A dermoscopic image of a skin lesion: 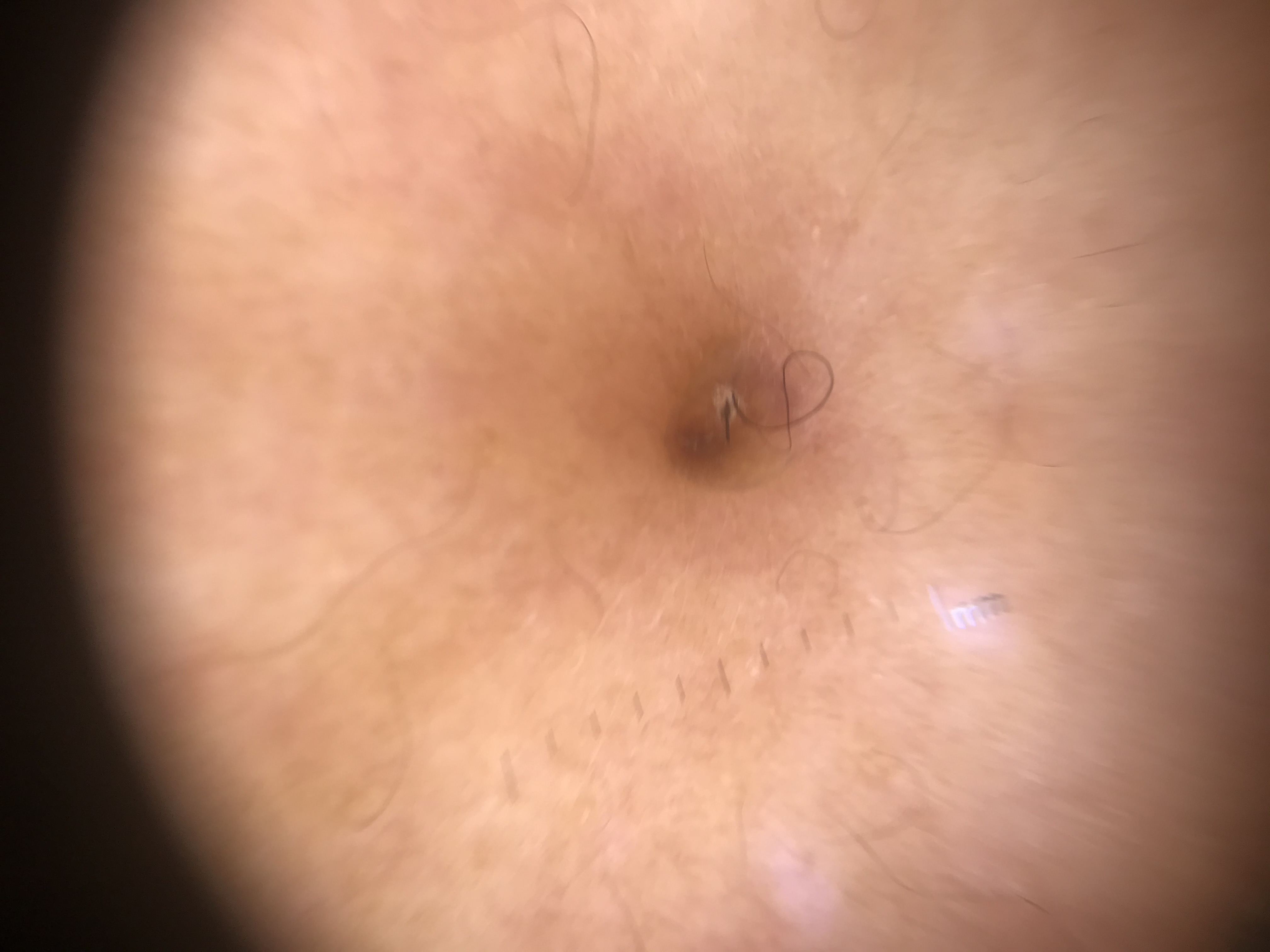diagnosis: dermal nevus (expert consensus).